A dermatoscopic image of a skin lesion: 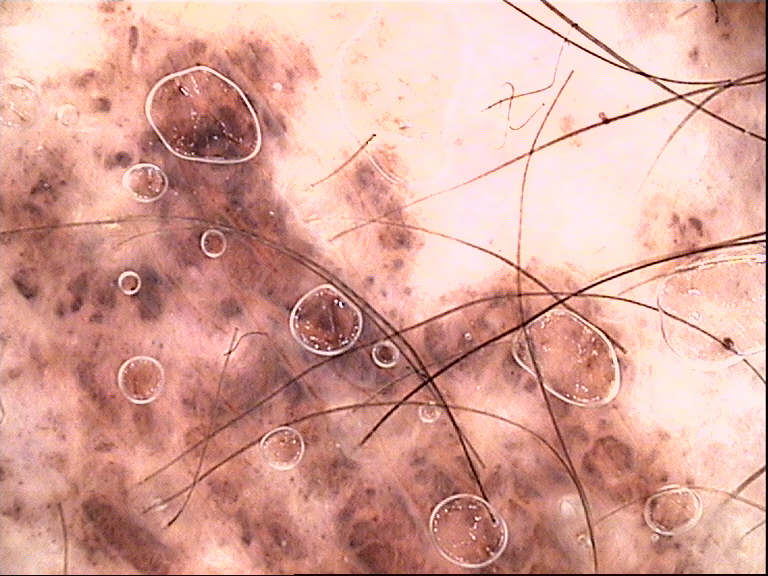Q: How is the lesion classified?
A: banal
Q: What is the diagnosis?
A: congenital compound nevus (expert consensus)